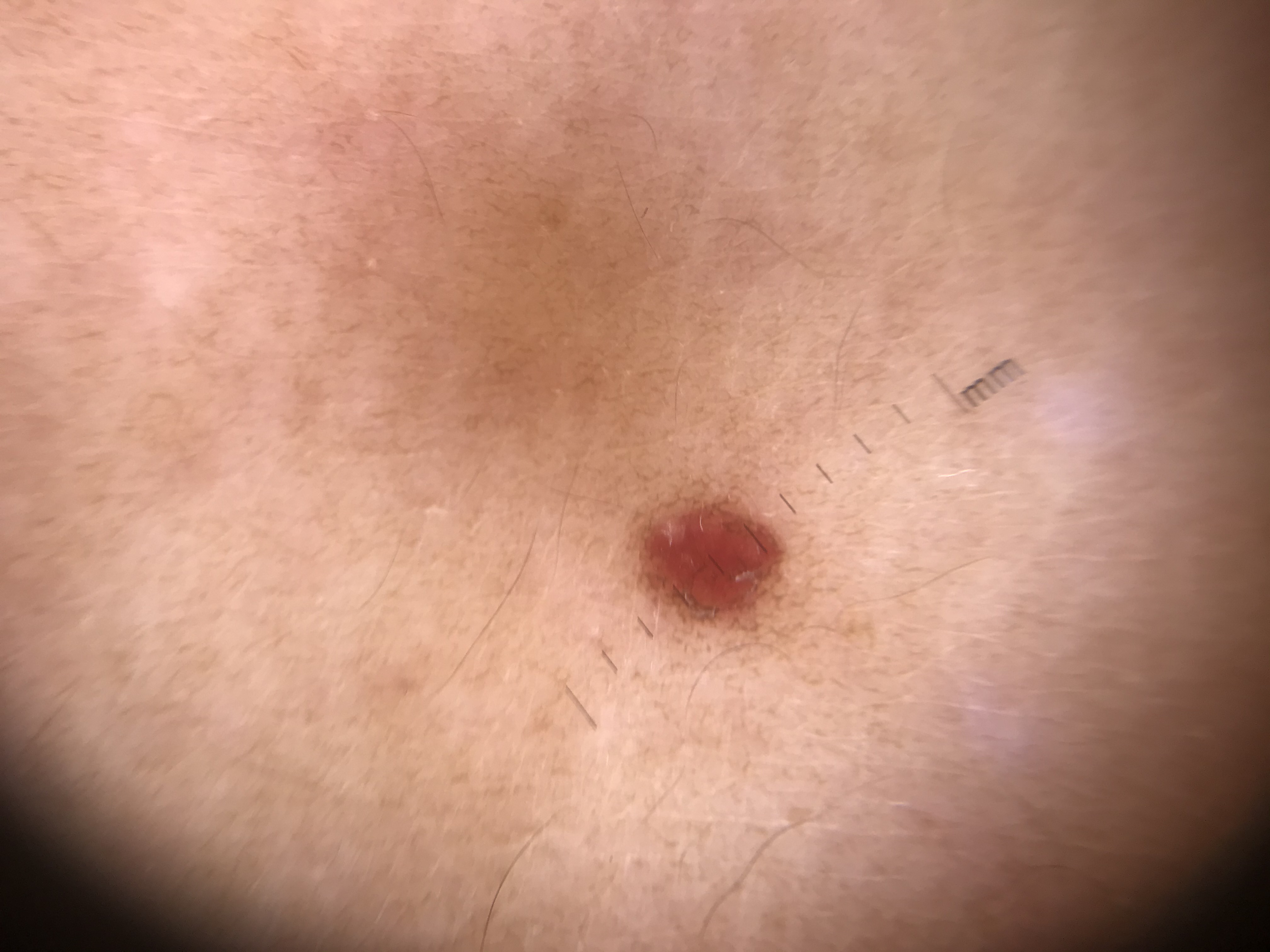| field | value |
|---|---|
| diagnostic label | hemangioma (expert consensus) |